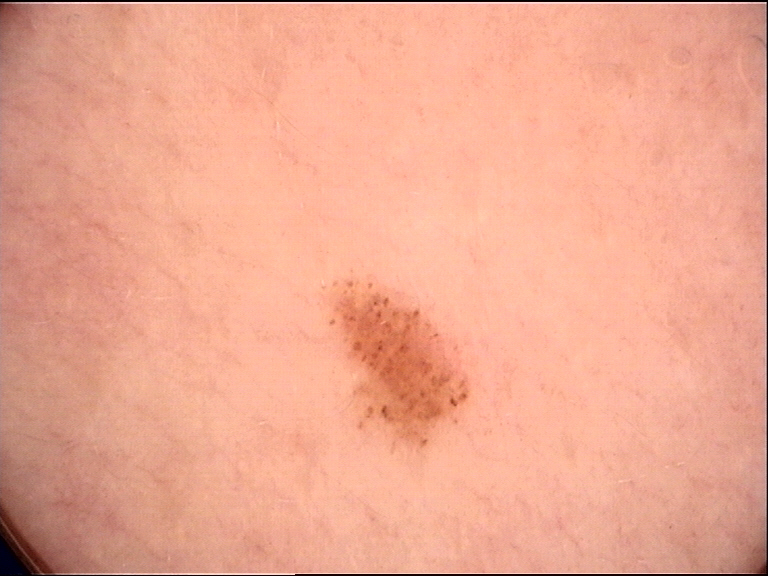Q: What is the imaging modality?
A: dermoscopy
Q: What was the diagnostic impression?
A: acral dysplastic junctional nevus (expert consensus)